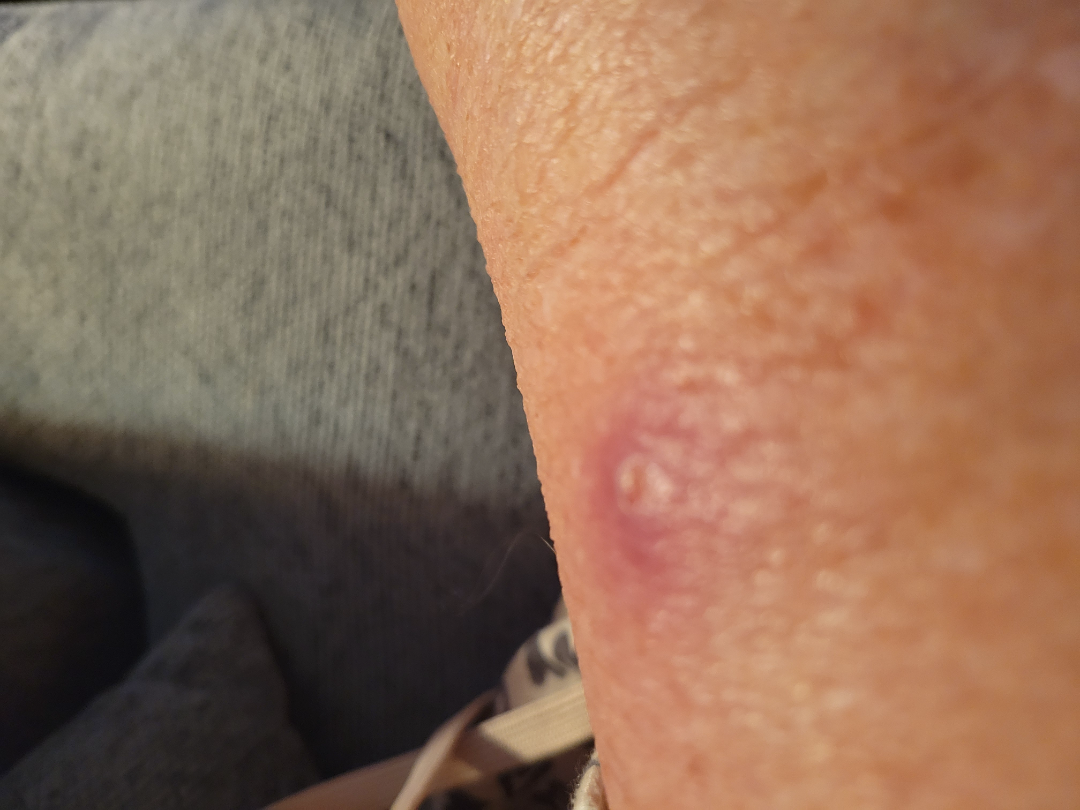Single-reviewer assessment: the differential includes Abscess and Insect Bite, with no clear leading consideration; less likely is SCC/SCCIS.